The contributor reports the lesion is raised or bumpy; the affected area is the back of the torso and front of the torso; associated systemic symptoms include joint pain and fatigue; a close-up photograph; the condition has been present for one to four weeks; the contributor is a female aged 50–59; self-categorized by the patient as a rash: 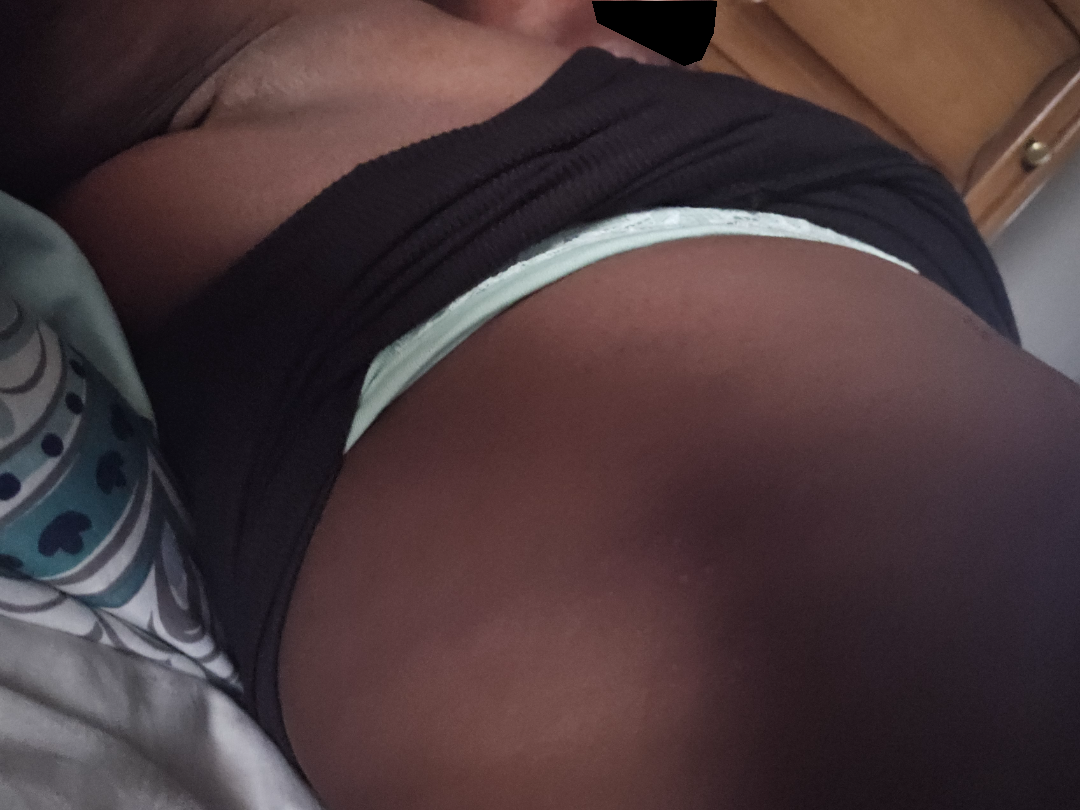The reviewing dermatologist was unable to assign a differential diagnosis from the image.